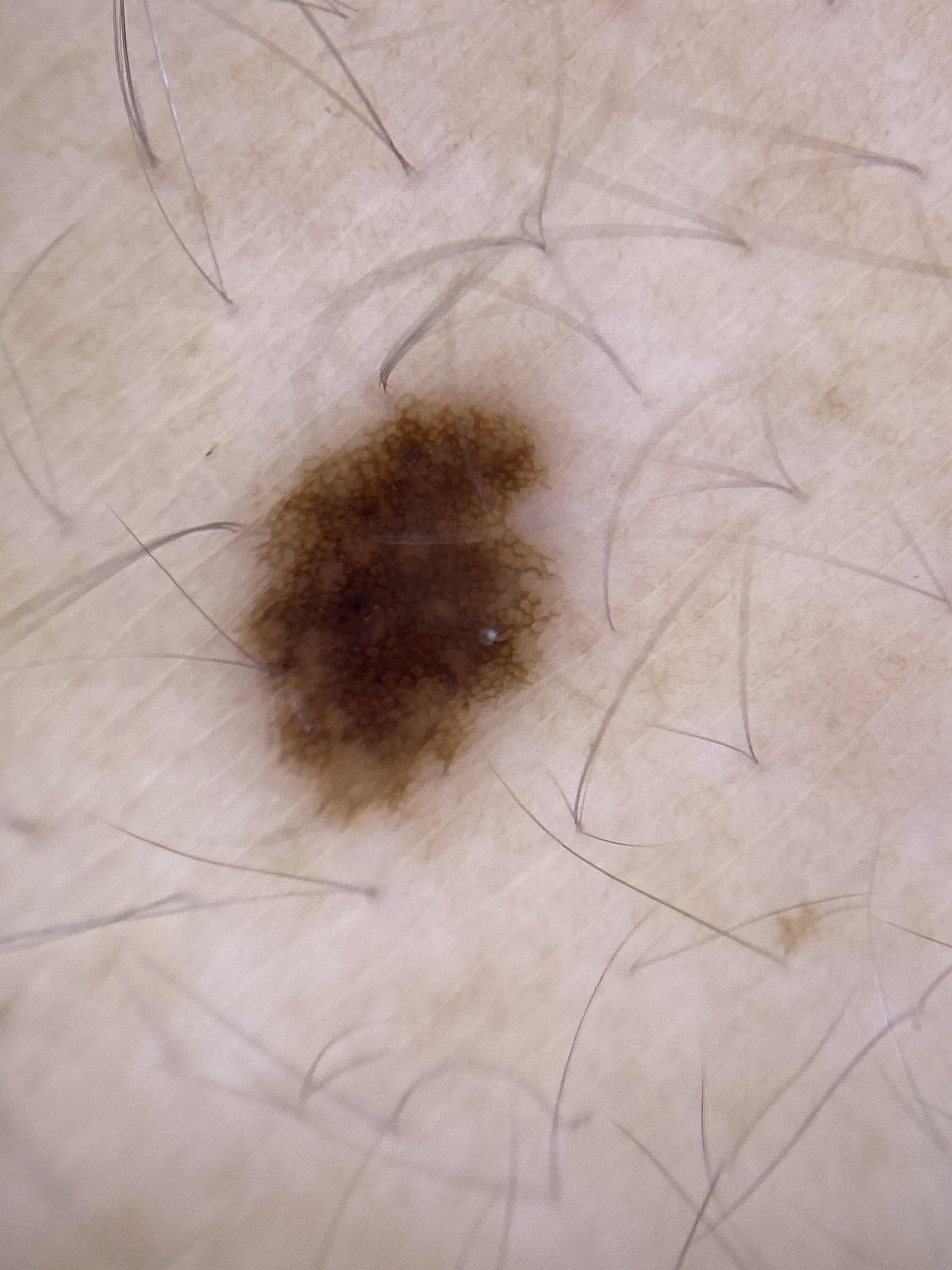skin type: II | subject: female, about 55 years old | modality: dermoscopy | body site: the trunk | diagnosis: Nevus (clinical impression).